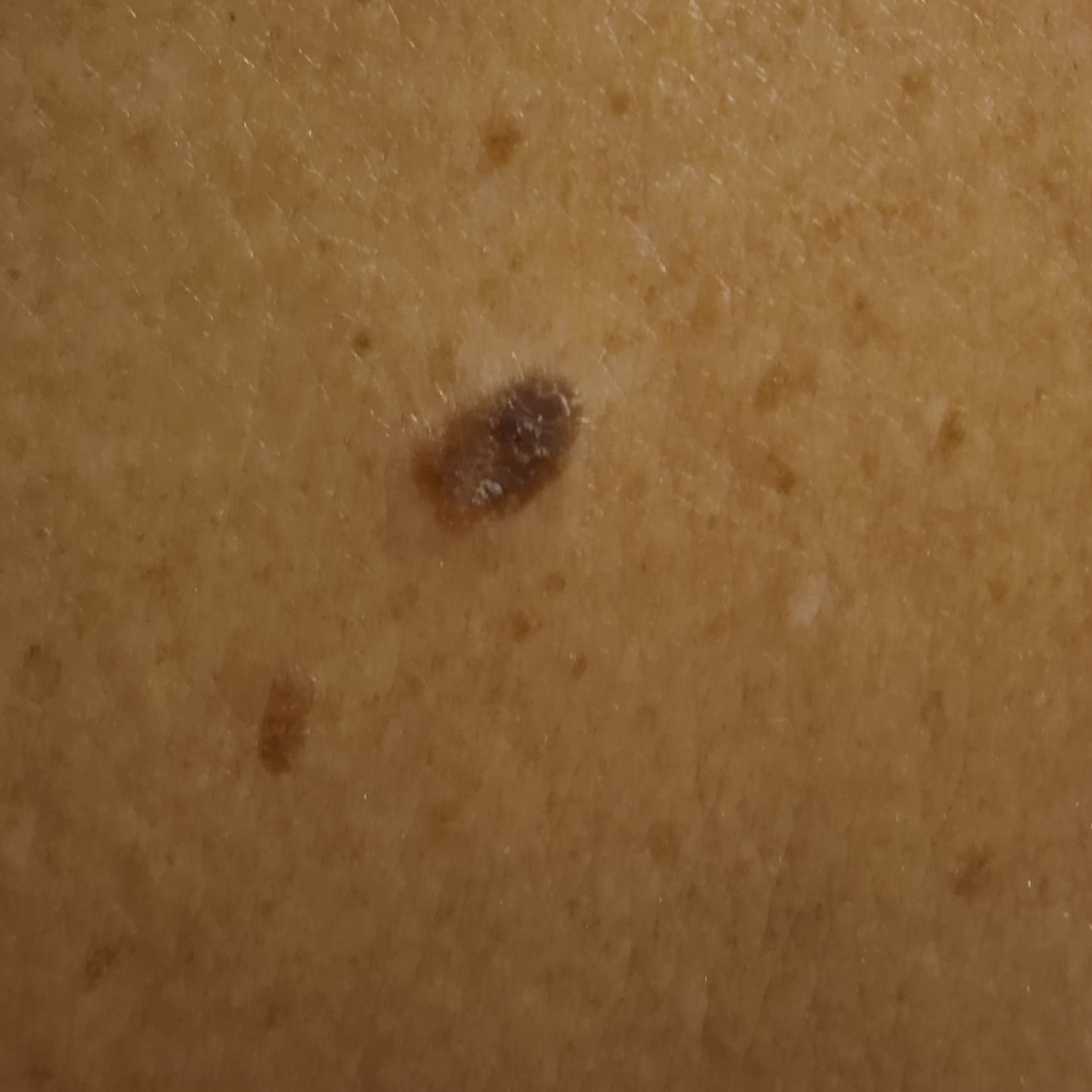The patient describes having a moderate number of moles.
Acquired for a research image collection, with no referral diagnosis.
A male subject age 72.
A clinical photograph of a skin lesion.
The patient says their skin tans without first burning.
The lesion is about 8.1 mm across.
The diagnostic impression was a seborrheic keratosis.